Dermoscopy of a skin lesion.
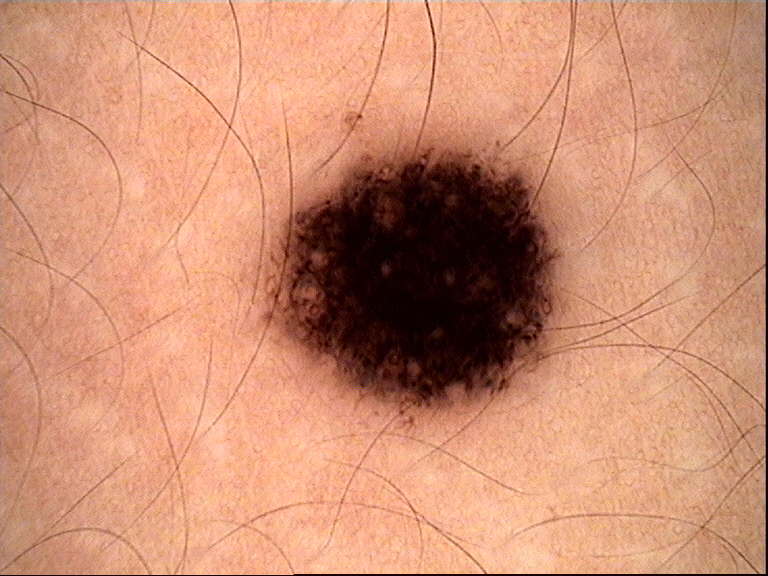diagnostic label = dysplastic compound nevus (expert consensus)